The photo was captured at an angle · the lesion involves the palm — 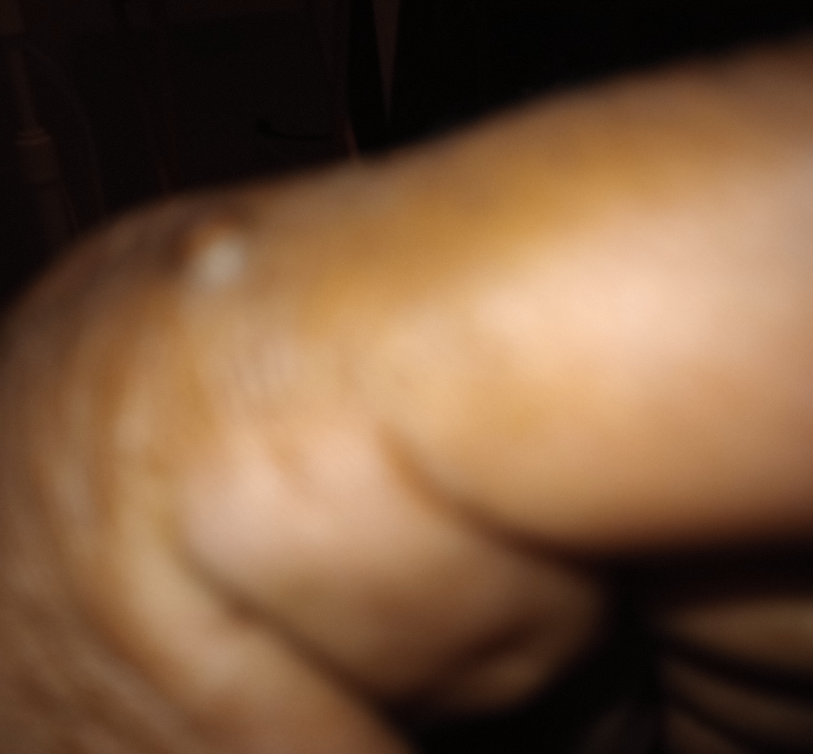clinical impression: Cyst (0.55); Dermatofibroma (0.27); Calcinosis cutis (0.18)